A clinical photograph of a skin lesion. A female patient aged 79:
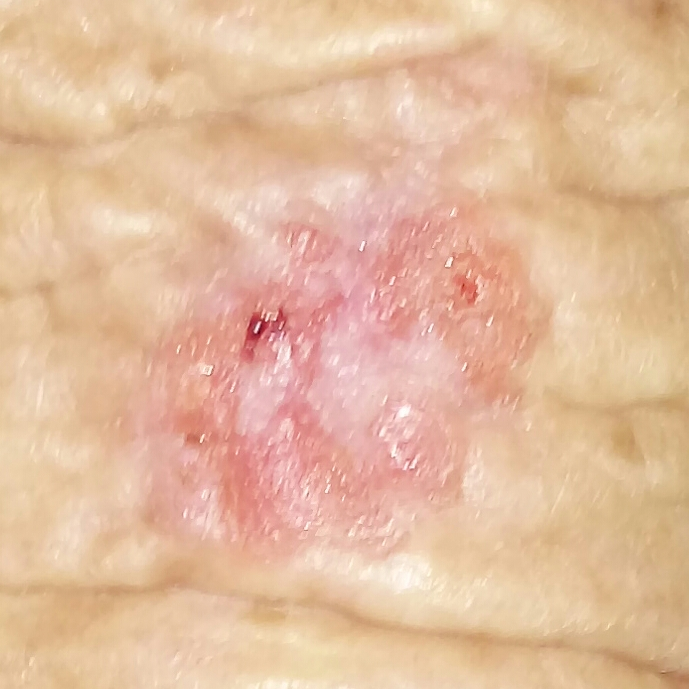Patient and lesion: The lesion involves an arm. The lesion measures 20 × 14 mm. Per patient report, the lesion itches and has bled. Diagnosis: Histopathological examination showed a squamous cell carcinoma.